A dermoscopic image of a skin lesion.
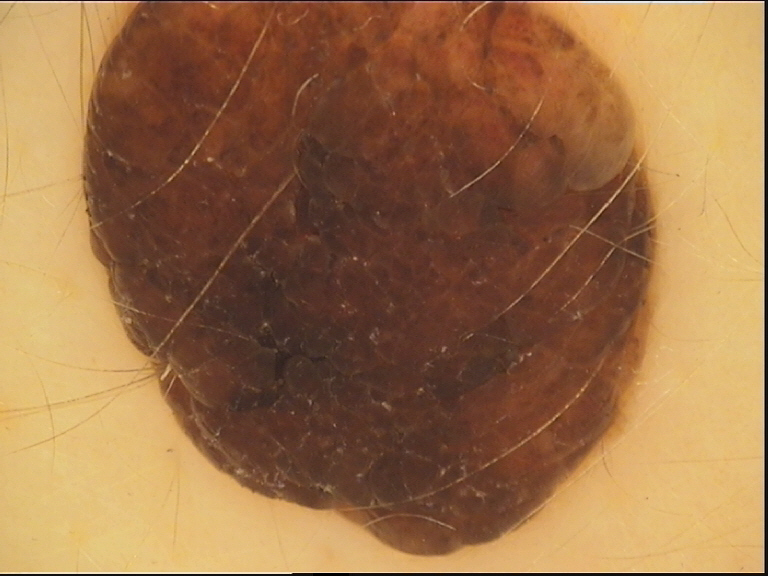The diagnosis was a banal lesion — a dermal nevus.